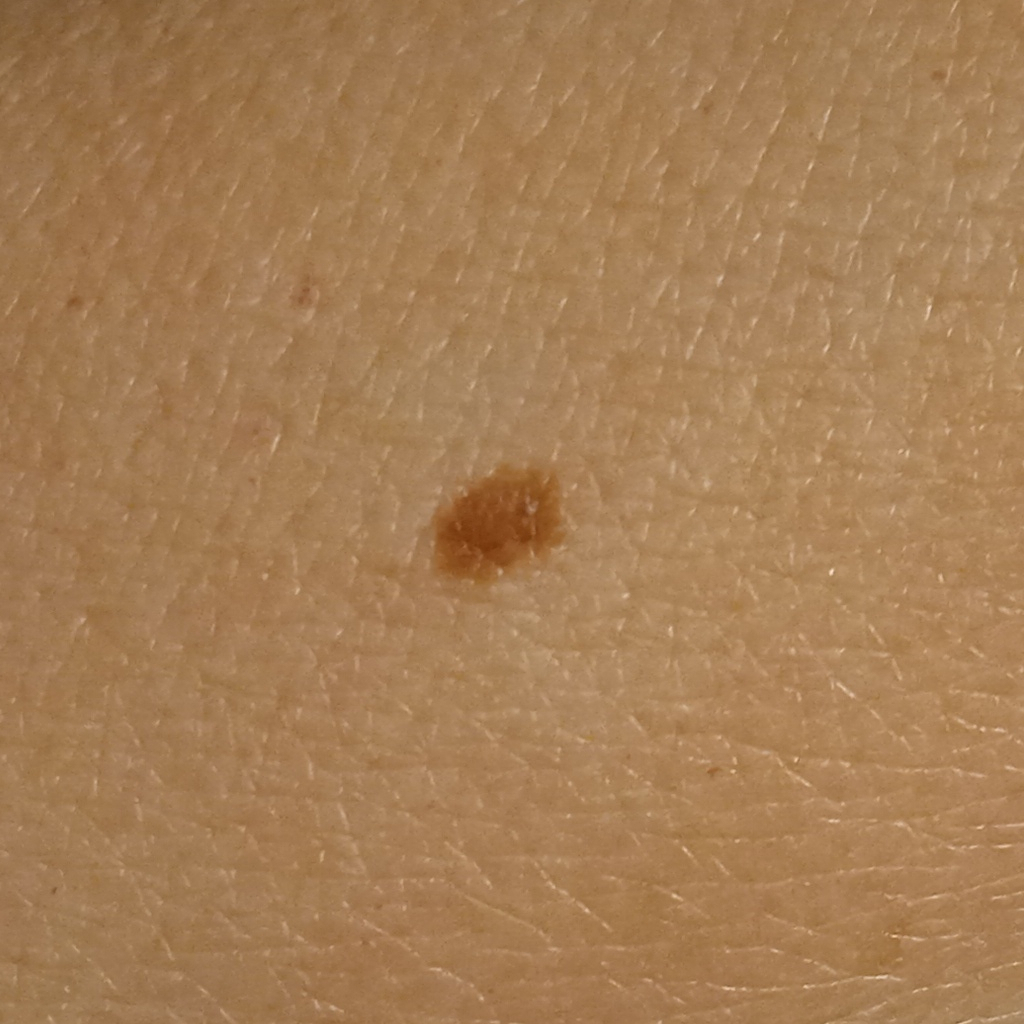The lesion was assessed as a melanocytic nevus.